Self-categorized by the patient as a rash · no constitutional symptoms were reported · skin tone: Fitzpatrick skin type III; lay graders estimated Monk skin tone scale 3 (US pool) or 2 (India pool) · female subject, age 40–49 · the photograph was taken at a distance · texture is reported as flat and raised or bumpy · reported duration is less than one week · the patient indicates itching and burning.
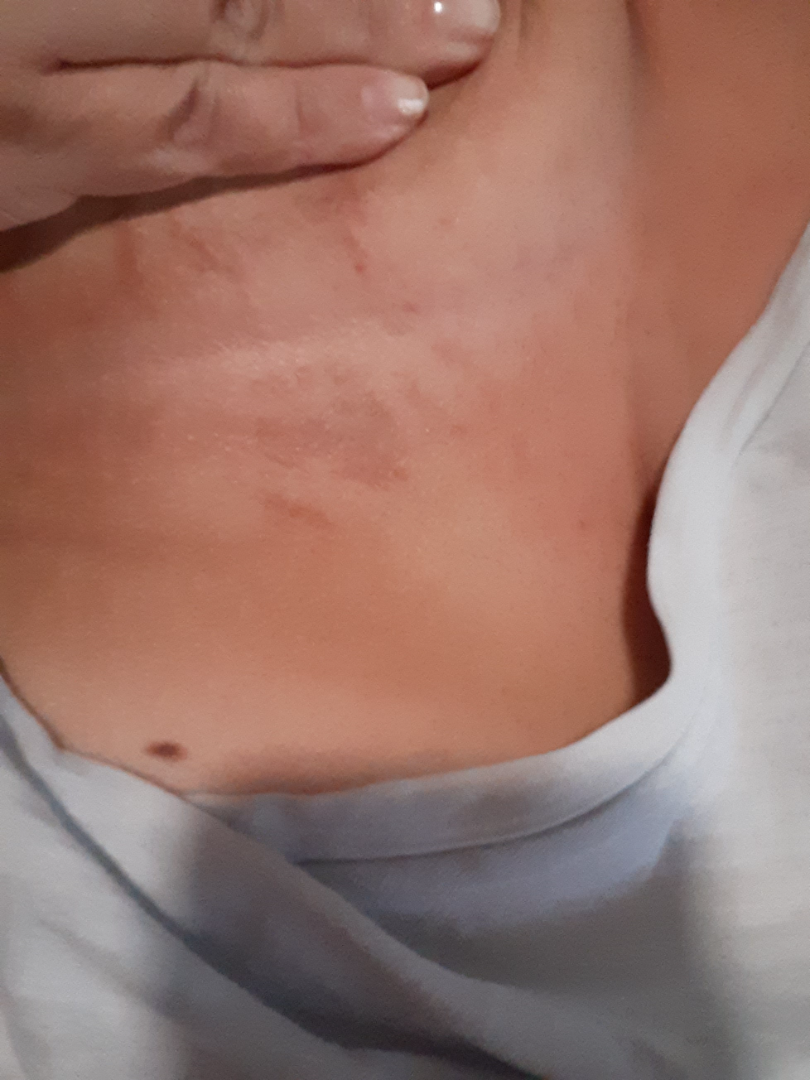Review:
A single dermatologist reviewed the case: most consistent with Eczema.